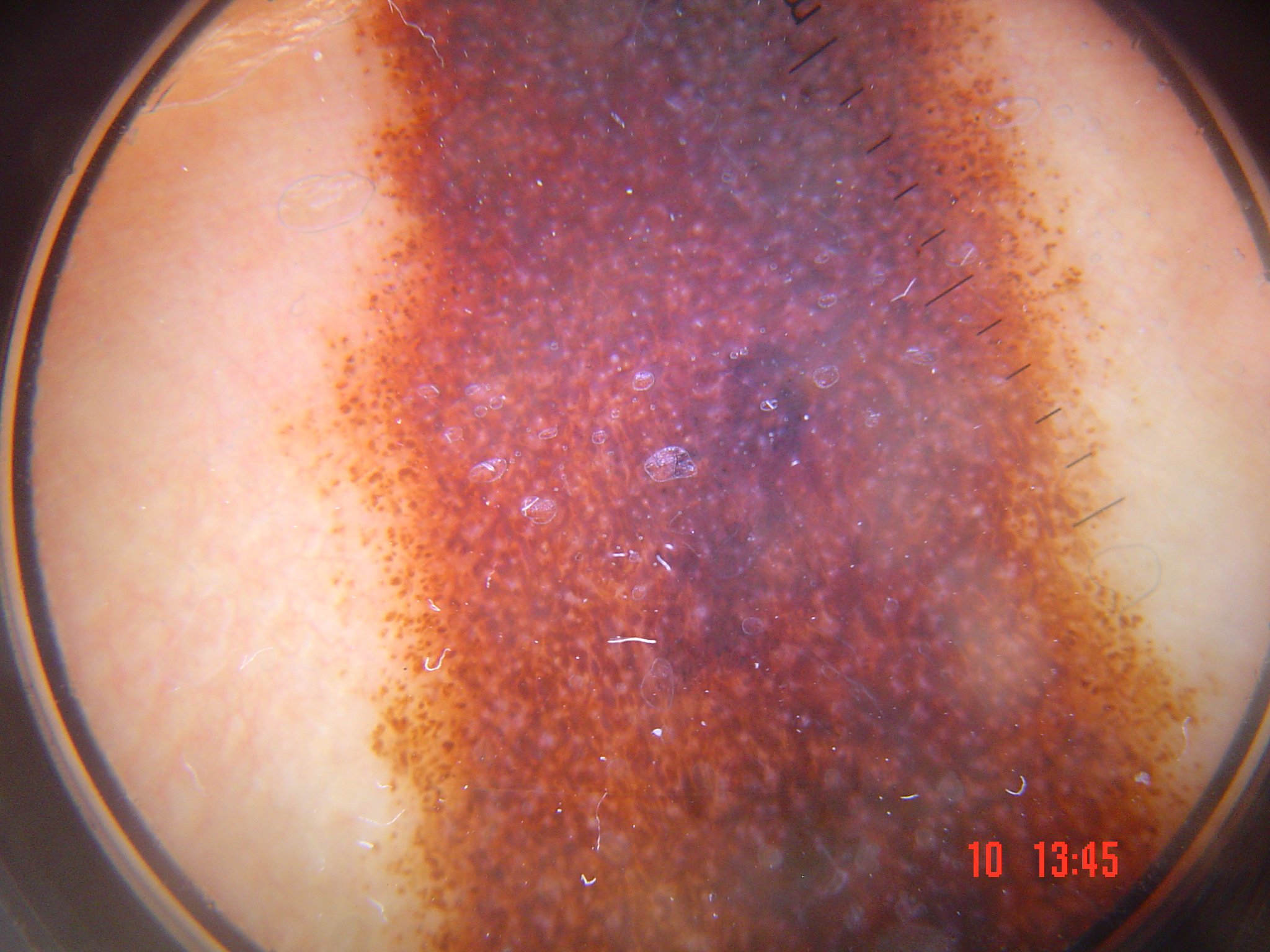Consistent with a congenital compound nevus.